Dermoscopy of a skin lesion:
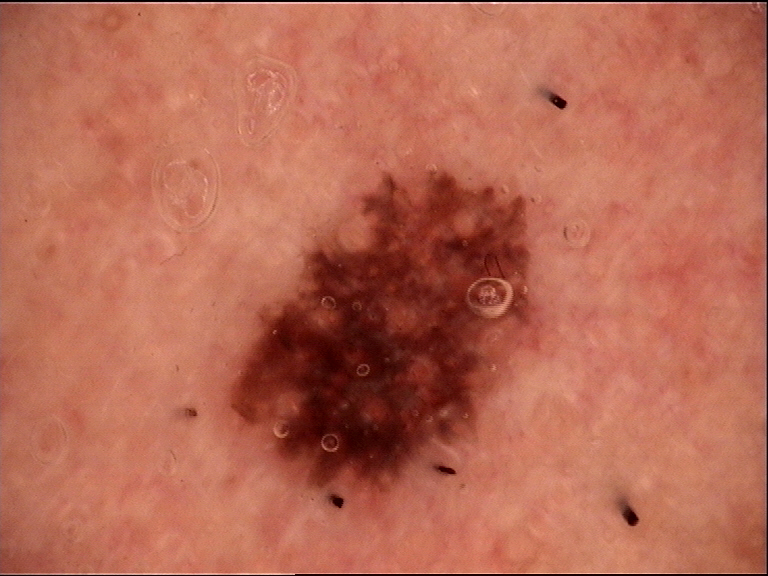Labeled as a dysplastic compound nevus.